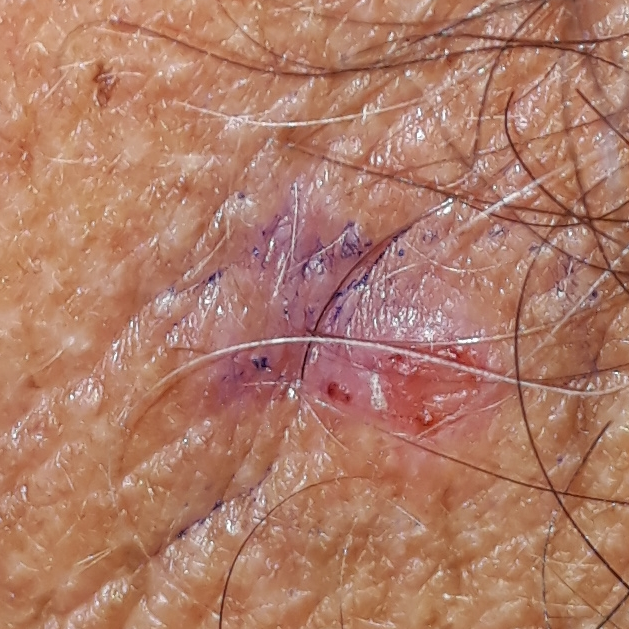A clinical close-up photograph of a skin lesion.
Recorded as skin type II.
A male subject 48 years of age.
The lesion was found on the neck.
The lesion measures approximately 5 × 5 mm.
The patient reports that the lesion itches, is elevated, and has bled.
On biopsy, the diagnosis was a basal cell carcinoma.